Close-up view:
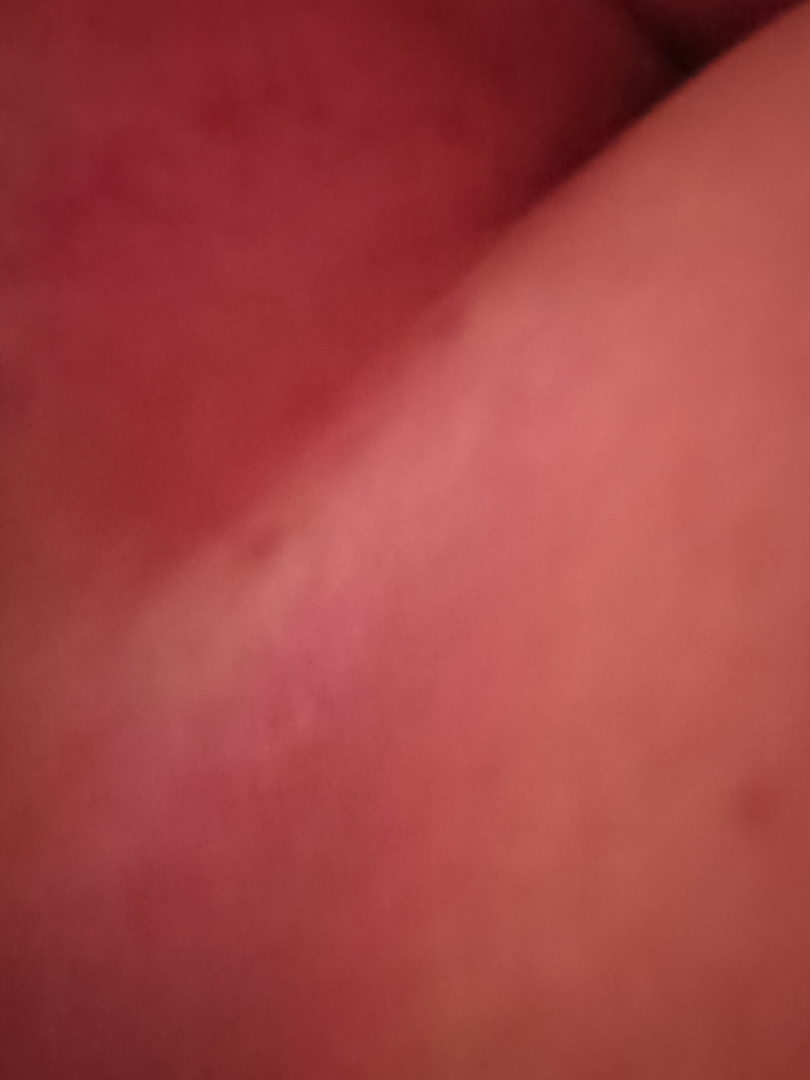The case was difficult to assess from the available photograph.